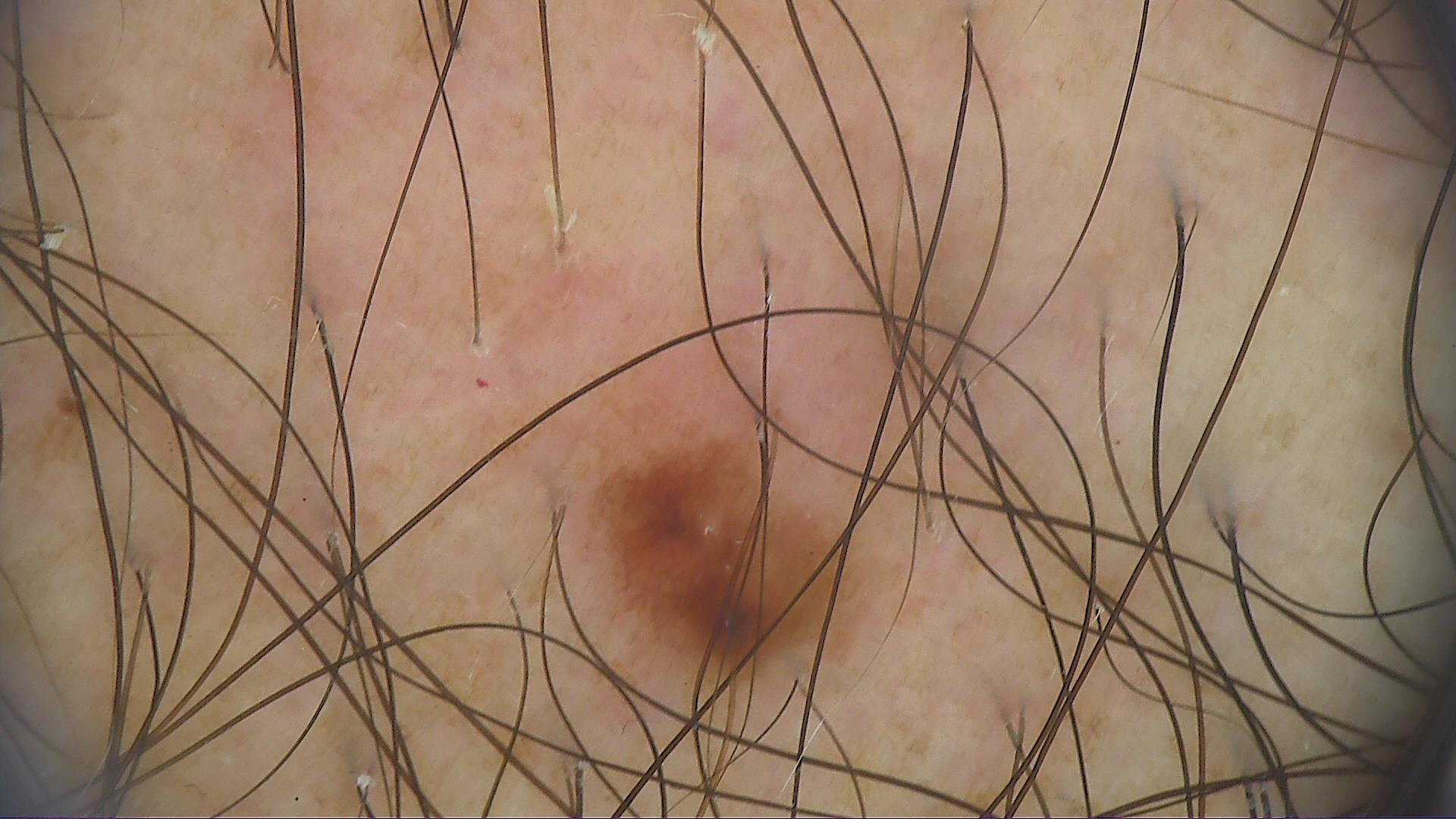diagnosis: dysplastic junctional nevus (expert consensus).